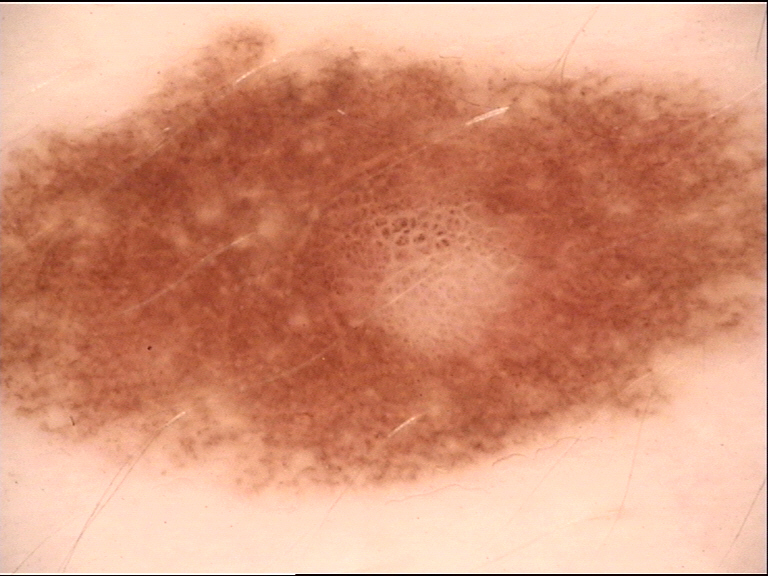imaging = dermatoscopy
class = dysplastic junctional nevus (expert consensus)